A clinical close-up photograph of a skin lesion. A male subject in their late 30s.
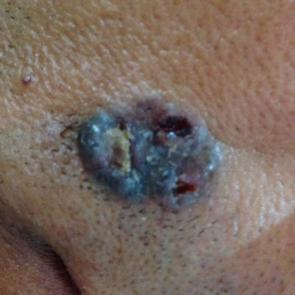lesion_location: the face
symptoms:
  present:
    - pain
    - bleeding
    - elevation
    - growth
    - itching
diagnosis:
  name: basal cell carcinoma
  code: BCC
  malignancy: malignant
  confirmation: histopathology